A clinical photograph showing a skin lesion. A patient aged 8.
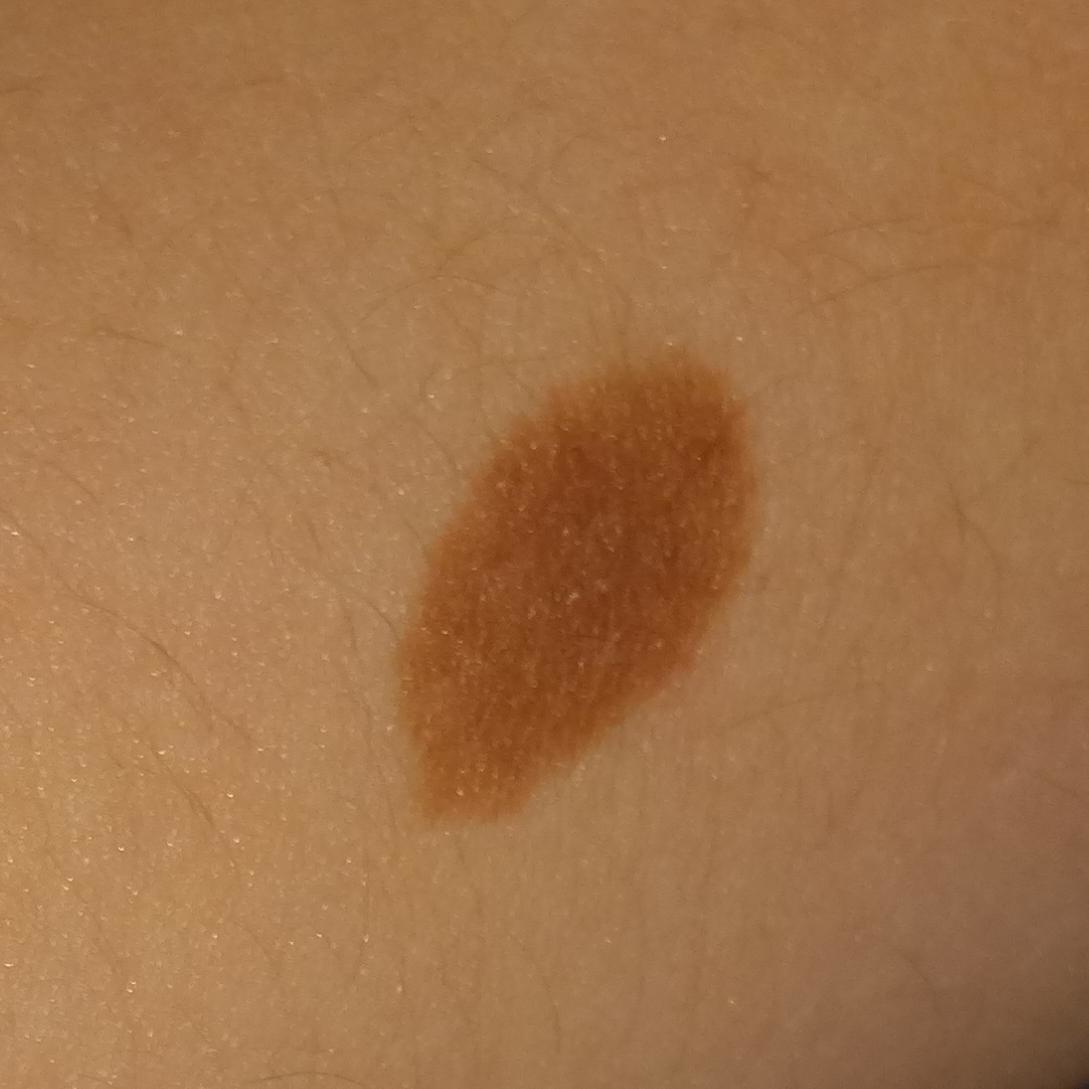Findings: The lesion is on an arm. No symptoms reported. Conclusion: Diagnosed by dermatologist consensus as a nevus.